A dermoscopic image of a skin lesion · a male subject aged 79 · the patient says their skin tans without first burning · acquired for a research image collection, with no referral diagnosis · few moles overall by the patient's own estimate: 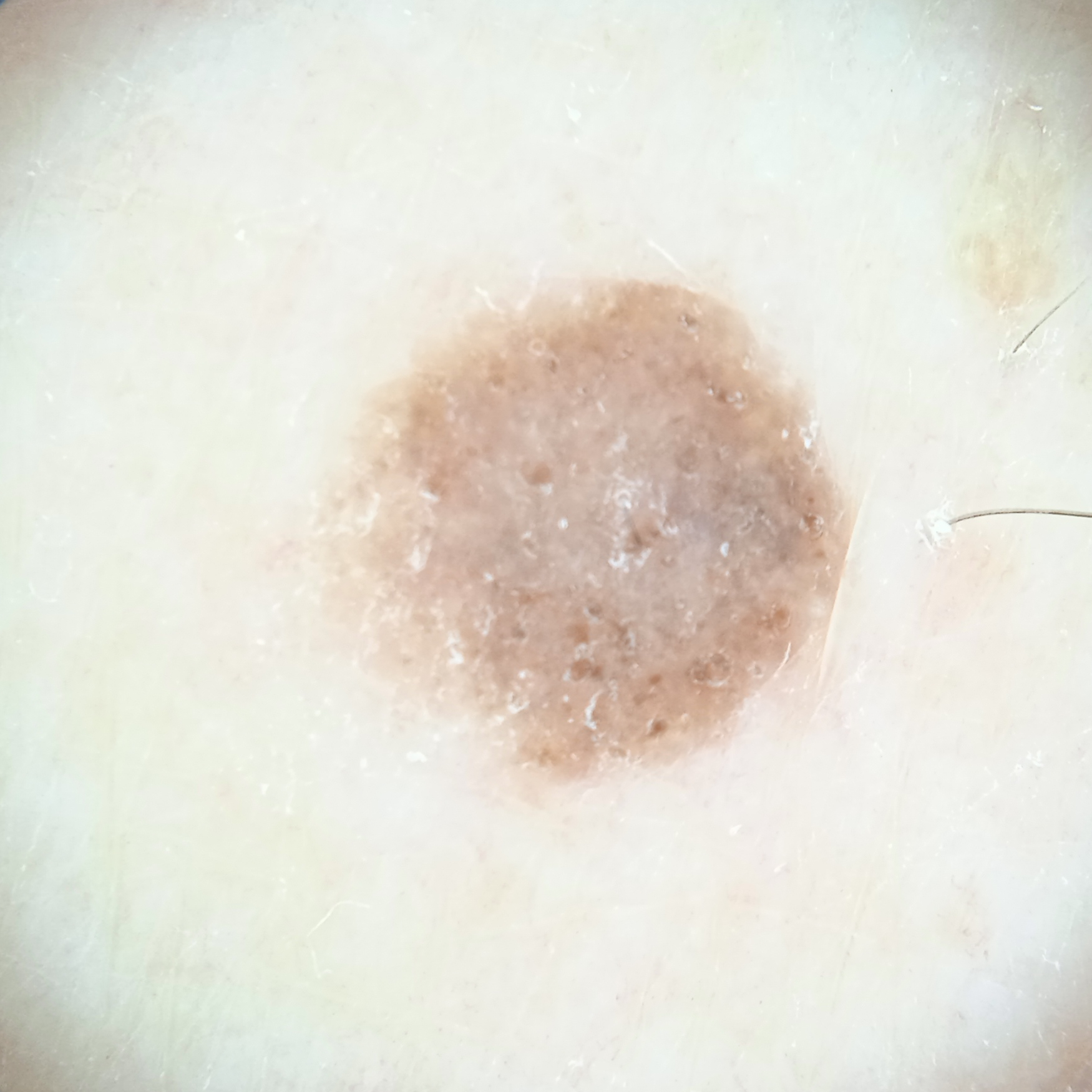Measuring roughly 5.8 mm. The dermatologists' assessment was a melanocytic nevus.